The contributor is a female aged 30–39; this is a close-up image; the lesion involves the leg: 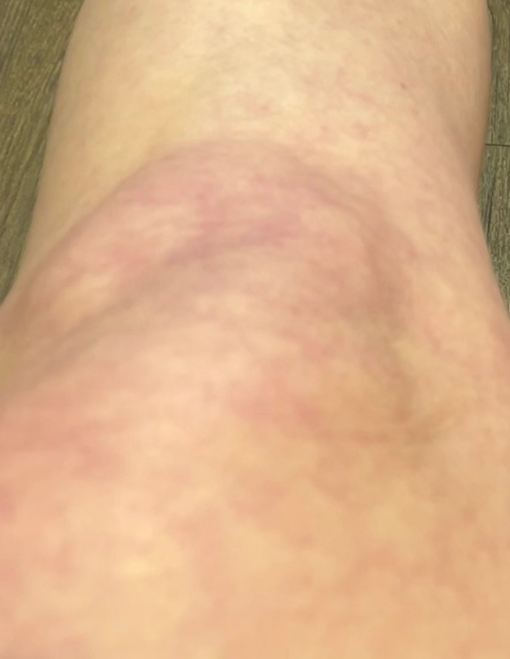The patient did not report lesion symptoms.
The patient described the issue as a rash.
Texture is reported as flat.
The contributor reports the condition has been present for more than five years.
Livedo reticularis (leading); Erythema ab igne (considered).